Female subject, age 18–29; this is a close-up image — 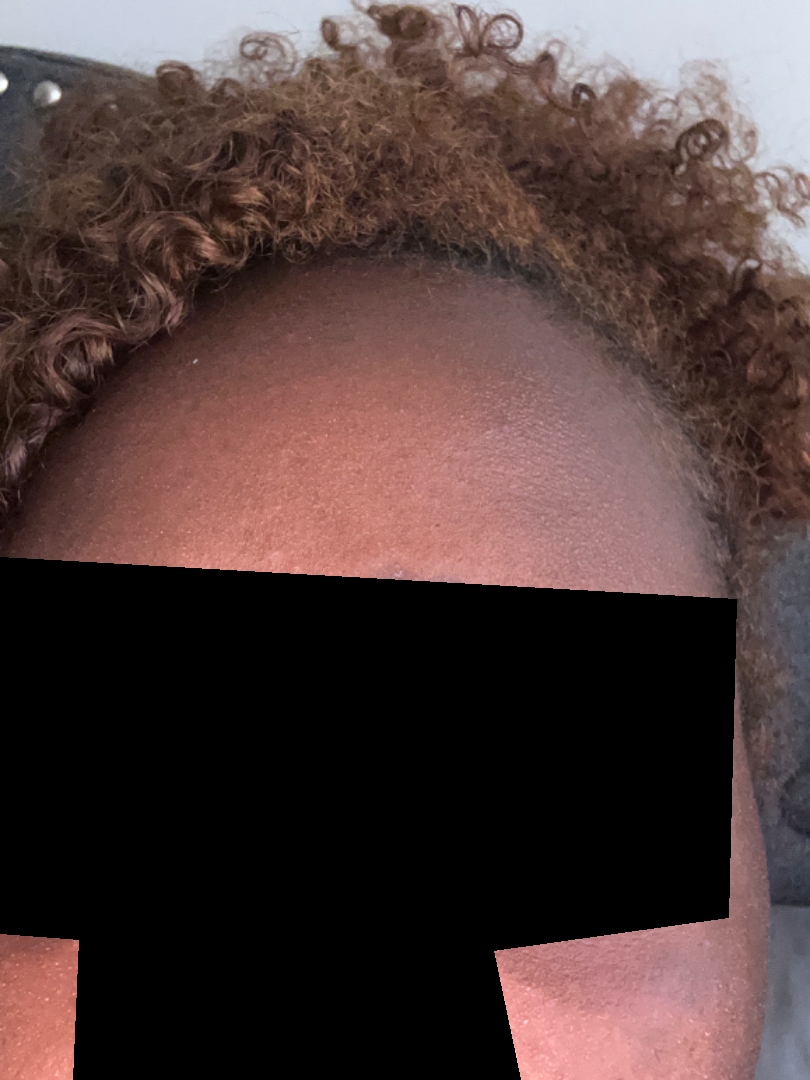present for — three to twelve months
dermatologist impression — Traction alopecia and Frontal fibrosing alopecia were each considered, in no particular order